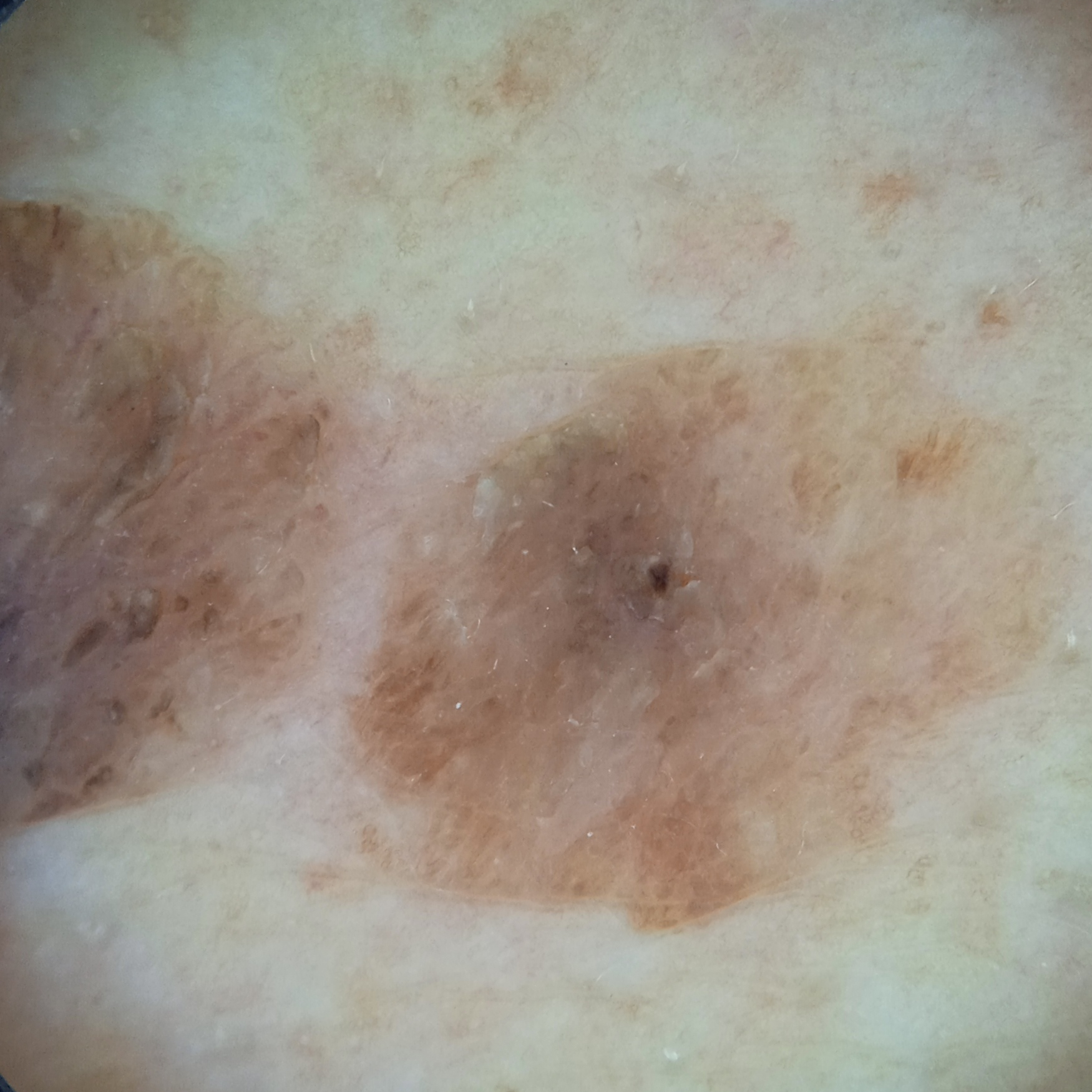nevus count = a moderate number of melanocytic nevi
subject = male, age 72
sun reaction = skin tans without first burning
referral = research study (no referral diagnosis)
image = dermoscopy
anatomic site = the back
lesion size = 12.8 mm
assessment = seborrheic keratosis (dermatologist consensus)